The lesion involves the head or neck, arm, front of the torso and back of the hand; a close-up photograph: 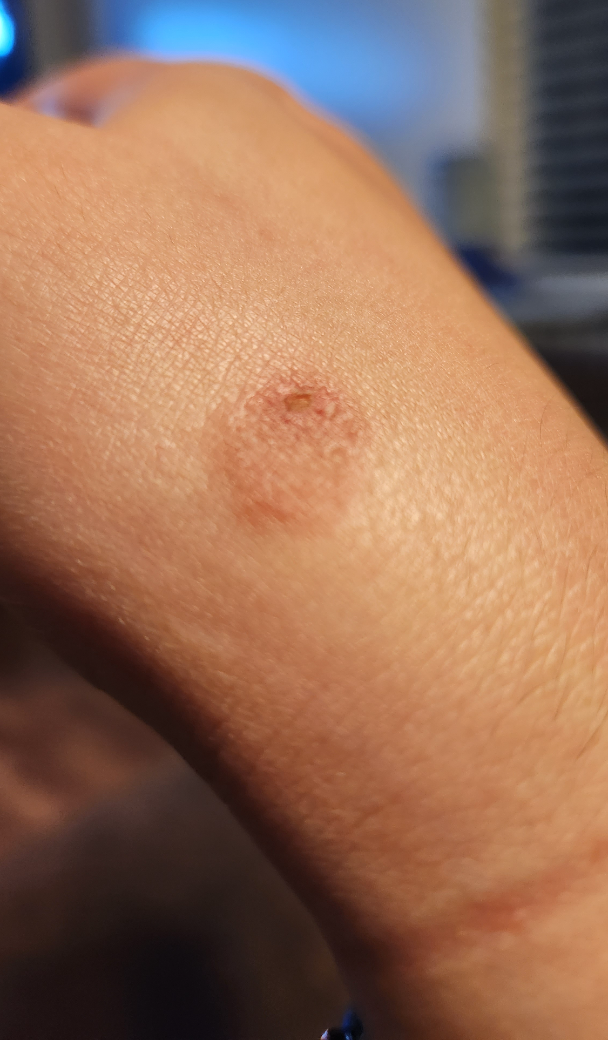- impression · Eczema (leading); Tinea (considered); Impetigo (lower probability); Allergic Contact Dermatitis (lower probability)